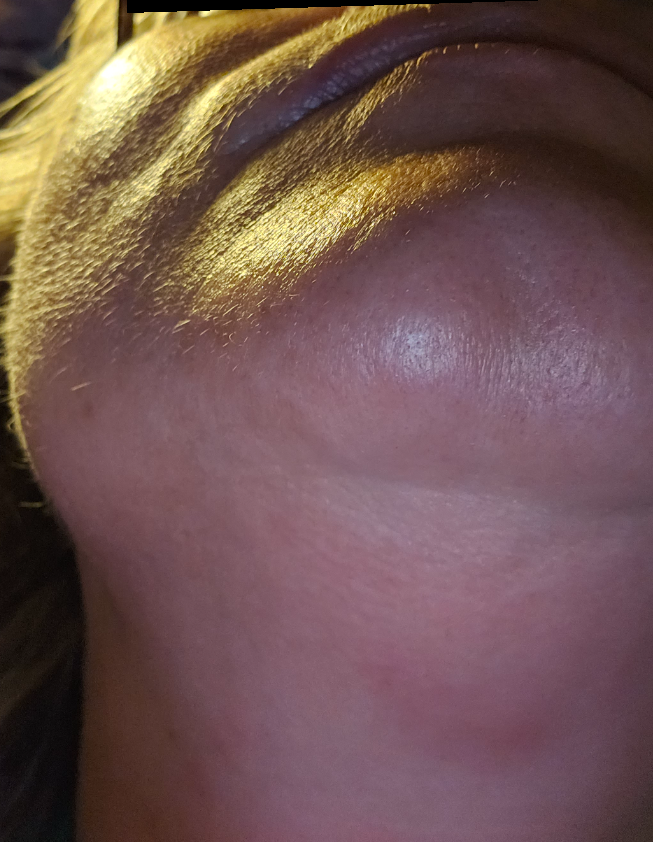{
  "assessment": "unable to determine",
  "skin_tone": {
    "fitzpatrick": "II",
    "monk_skin_tone": 2
  },
  "duration": "less than one week",
  "body_site": [
    "arm",
    "palm",
    "back of the hand",
    "head or neck",
    "leg"
  ],
  "patient_category": "a rash",
  "shot_type": "close-up",
  "patient": "female, age 40–49",
  "texture": "raised or bumpy",
  "symptoms": [
    "enlargement",
    "itching"
  ],
  "systemic_symptoms": "none reported"
}